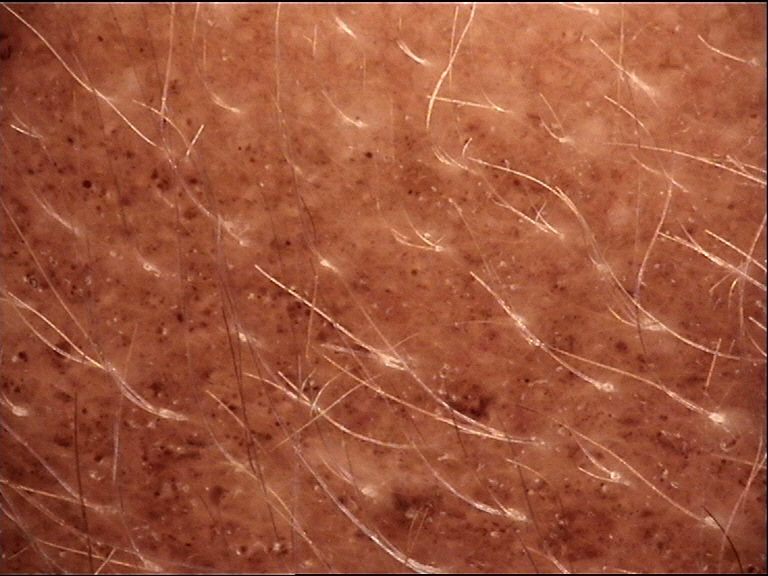assessment = congenital compound nevus (expert consensus).